The contributor notes burning. The contributor notes the condition has been present for less than one week. The leg is involved. Texture is reported as rough or flaky and raised or bumpy. Female patient, age 40–49. This is a close-up image — 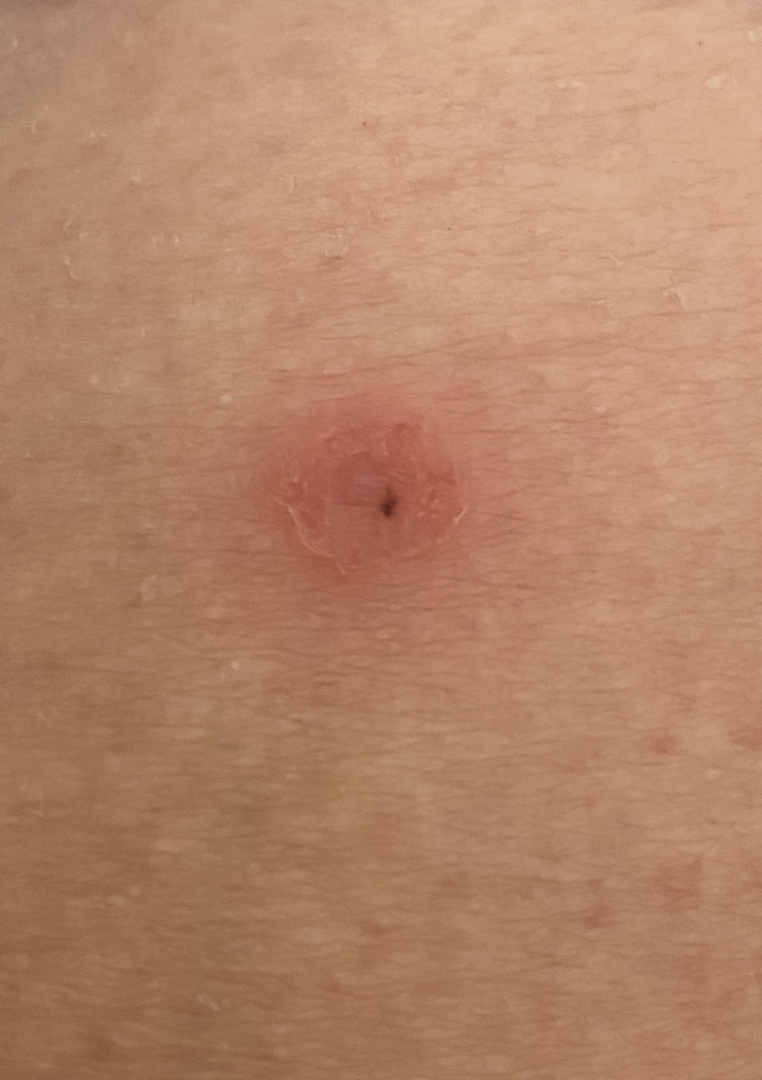Findings: No differential diagnosis could be assigned on photographic review.